Reported duration is less than one week · the photo was captured at a distance · the lesion is described as raised or bumpy · the affected area is the leg · Fitzpatrick phototype III · the lesion is associated with enlargement and burning.
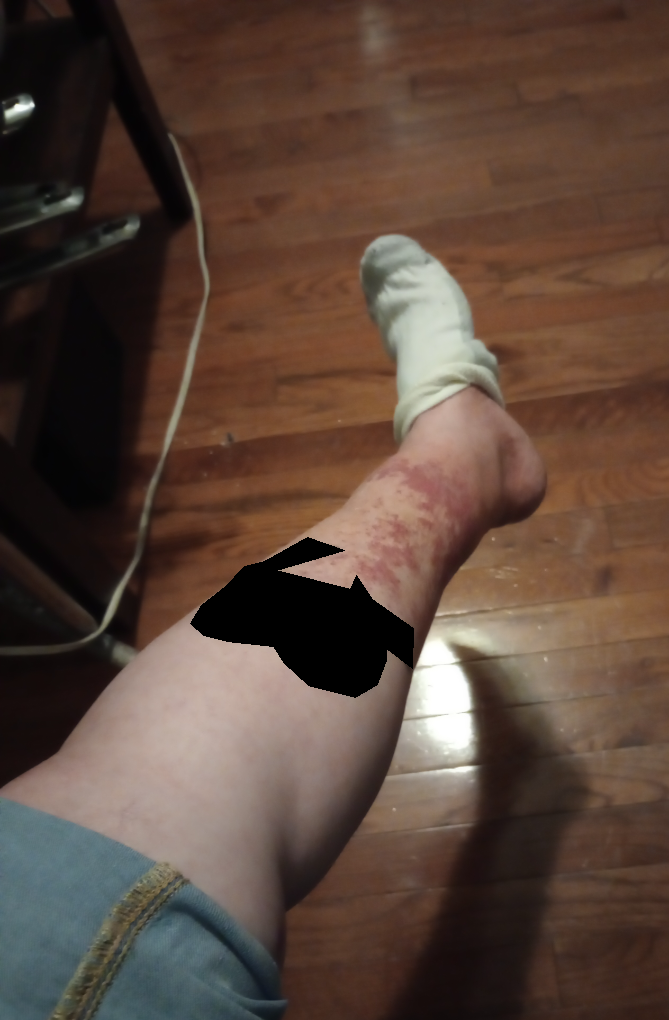{"differential": {"tied_lead": ["Photodermatitis", "Eczema", "Irritant Contact Dermatitis"]}}